A subject in their early 60s. A clinical photograph of a skin lesion: 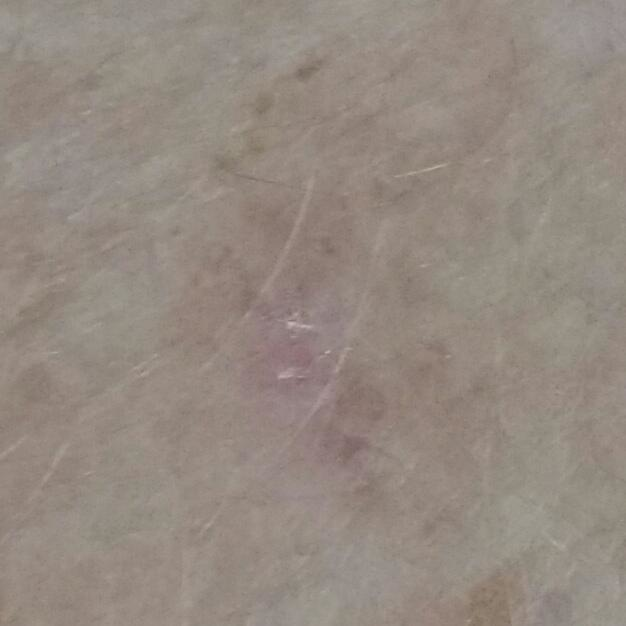Findings: The lesion was found on a forearm. The patient describes that the lesion does not hurt and has not bled. Impression: Diagnosed by dermatologist consensus as an actinic keratosis.